A dermoscopic photograph of a skin lesion.
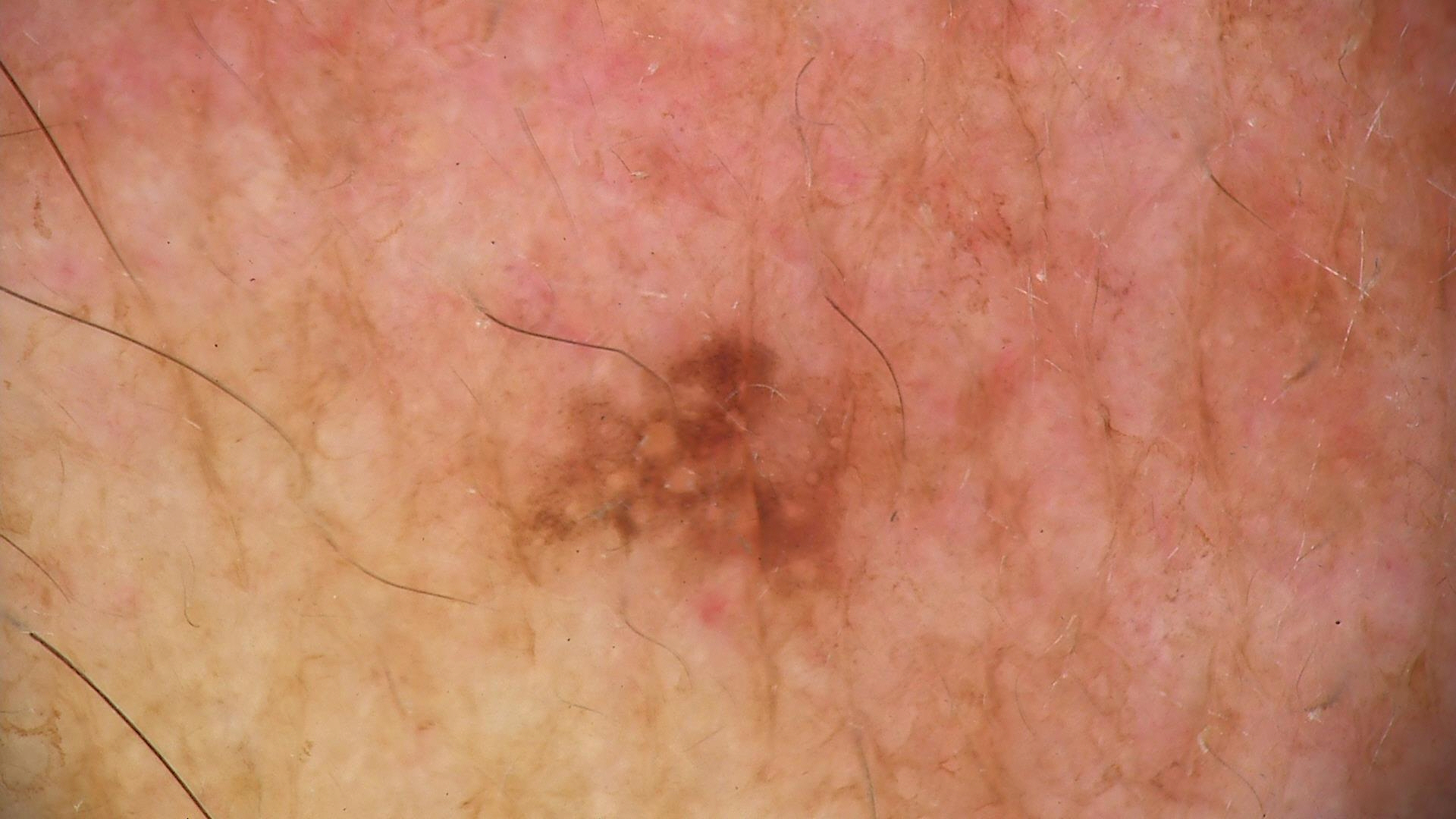Conclusion: The diagnosis was a keratinocytic lesion — a seborrheic keratosis.